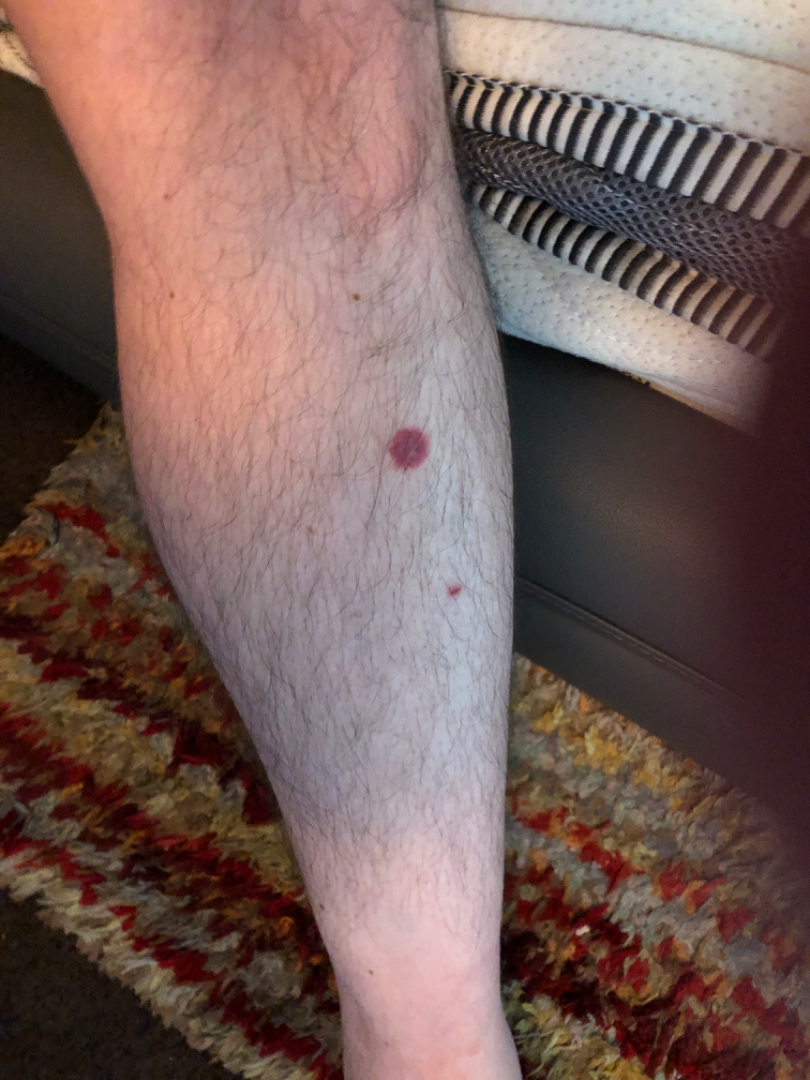{"patient": "male, age 50–59", "duration": "about one day", "symptoms": "bothersome appearance", "body_site": "leg", "systemic_symptoms": "none reported", "texture": "flat", "skin_tone": {"fitzpatrick": "I", "monk_skin_tone": [1, 2]}, "shot_type": "at a distance", "differential": {"tied_lead": ["Insect Bite", "Cutaneous sarcoidosis", "Leukocytoclastic Vasculitis"]}}